A dermoscopic image of a skin lesion.
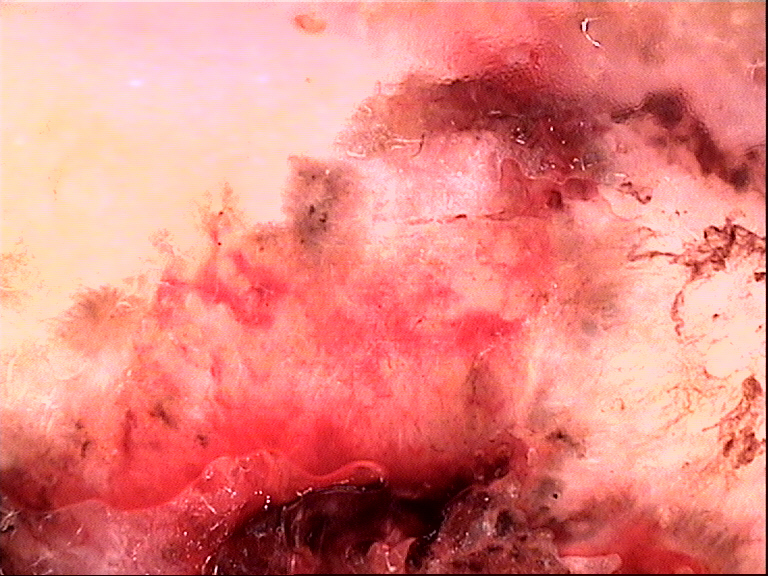Q: How is the lesion classified?
A: keratinocytic
Q: What is the diagnosis?
A: basal cell carcinoma (biopsy-proven)